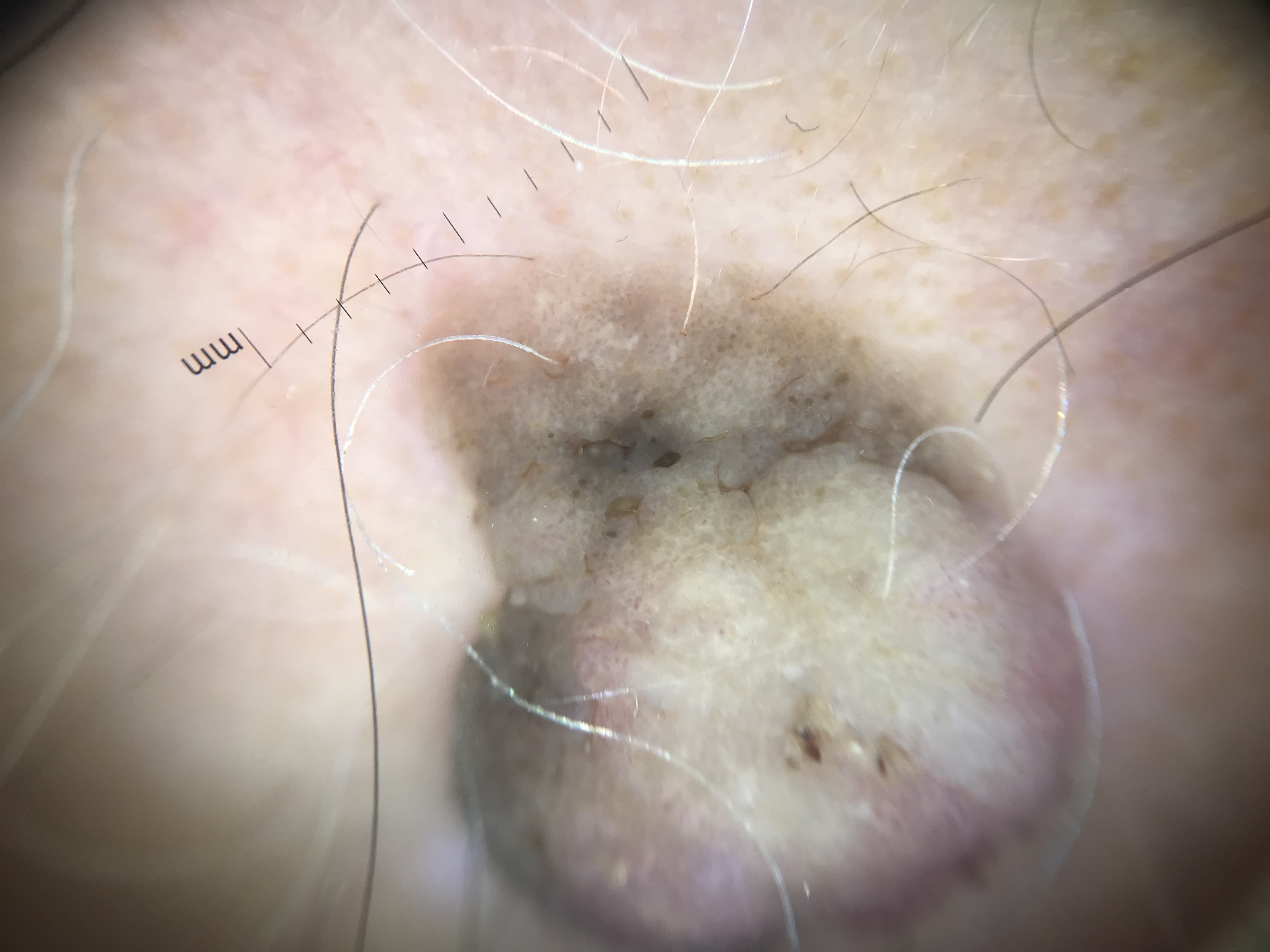Impression: Consistent with a seborrheic keratosis.